Dermoscopy of a skin lesion; a female patient age 75; acquired for a research image collection, with no referral diagnosis:
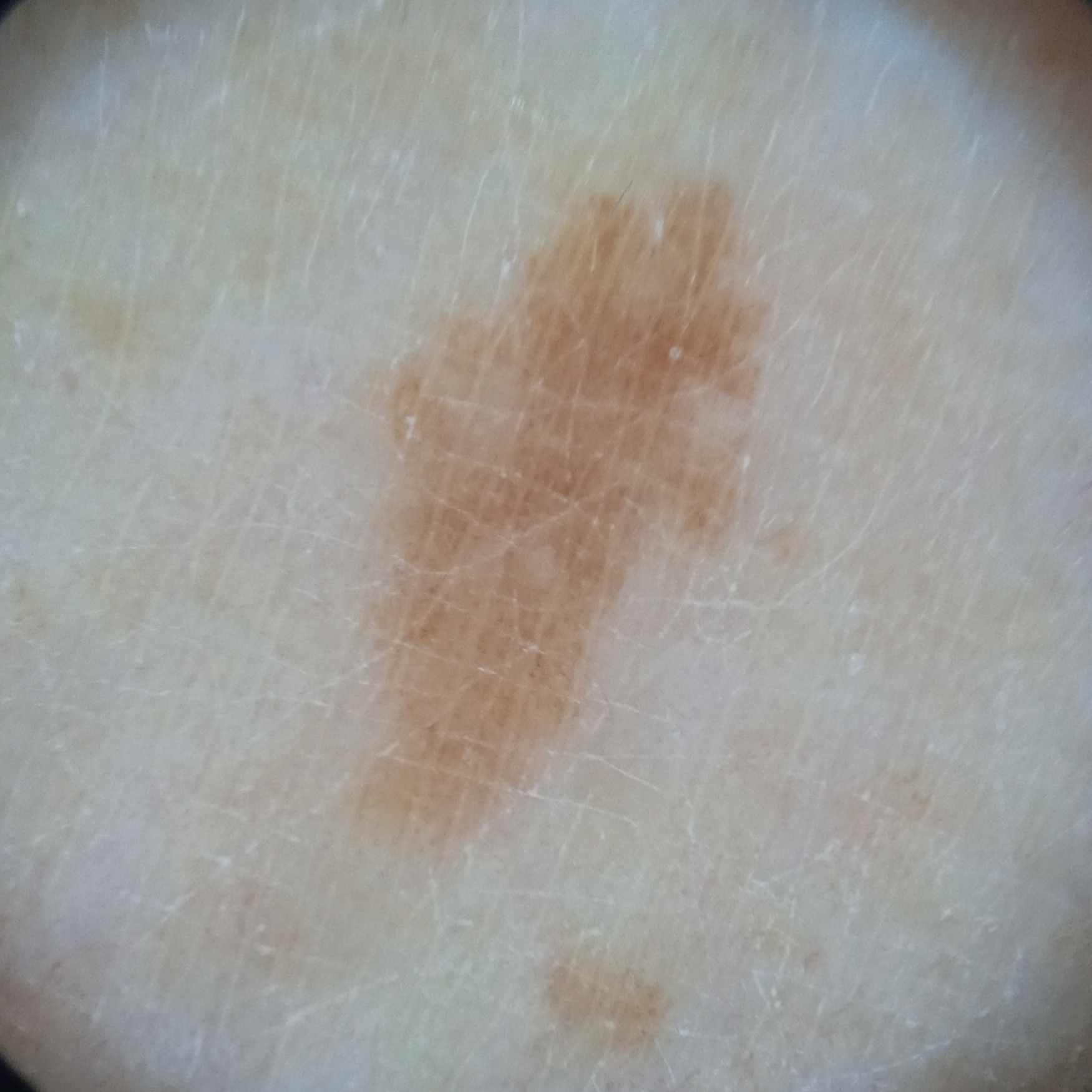Clinical context: Located on a leg. The lesion measures approximately 8.2 mm. Assessment: The diagnostic impression was a melanocytic nevus.